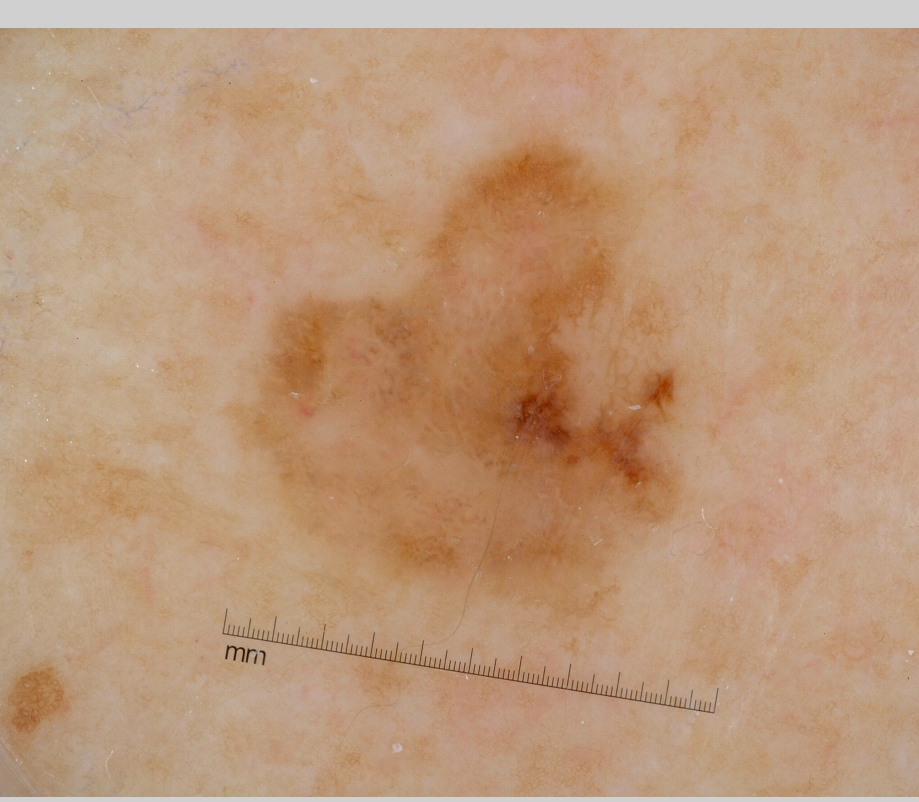Dermoscopy of a skin lesion. With coordinates (x1, y1, x2, y2), the lesion is bounded by [245, 133, 685, 620]. Histopathologically confirmed as a melanoma, a skin cancer.